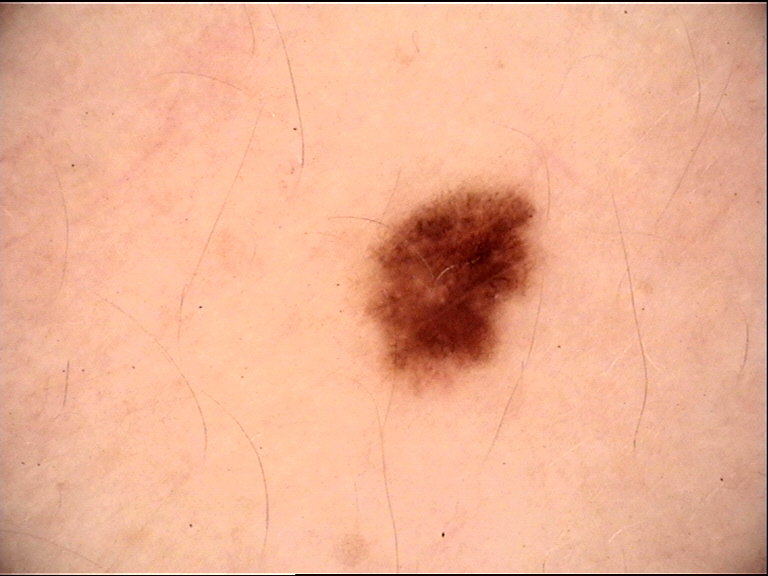A skin lesion imaged with a dermatoscope. Diagnosed as a dysplastic junctional nevus.